The affected area is the back of the hand, arm and front of the torso · the lesion is described as rough or flaky and raised or bumpy · this image was taken at an angle · the contributor reports itching and enlargement · no relevant systemic symptoms:
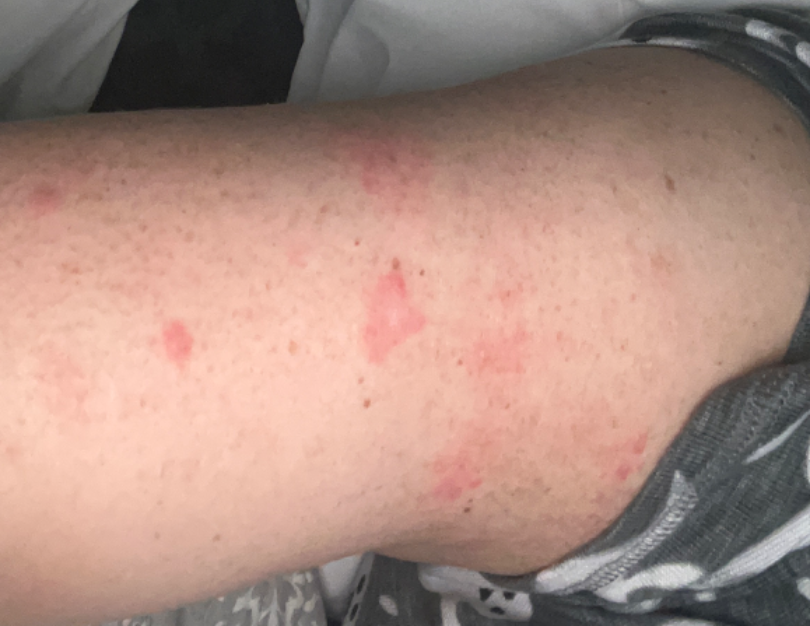Review: The differential includes Impetigo; Photodermatitis; and Acute dermatitis, NOS, with no clear leading consideration.